An image taken at a distance. The lesion involves the back of the torso, leg and arm. The subject is a female aged 60–69.
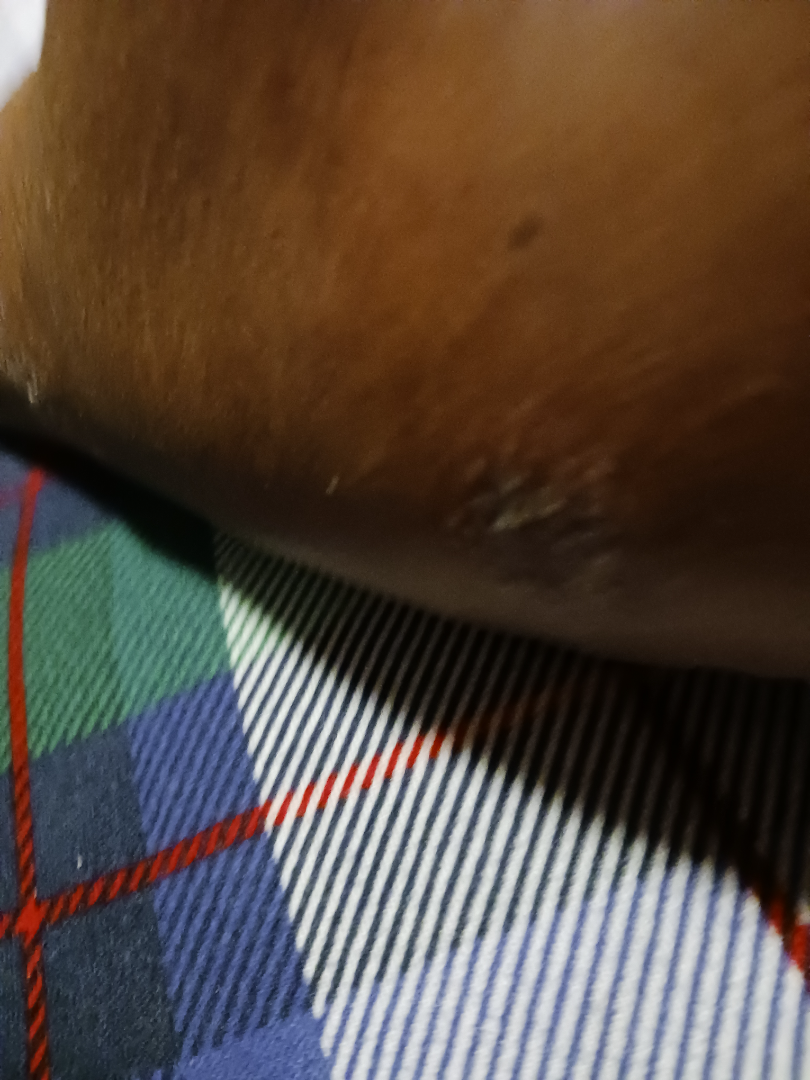Findings:
• constitutional symptoms · none reported
• reported symptoms · enlargement, itching, darkening and burning
• history · one to three months
• surface texture · raised or bumpy and rough or flaky
• patient describes the issue as · a rash
• impression · favoring Eczema; also consider Stasis Dermatitis; less likely is Psoriasis